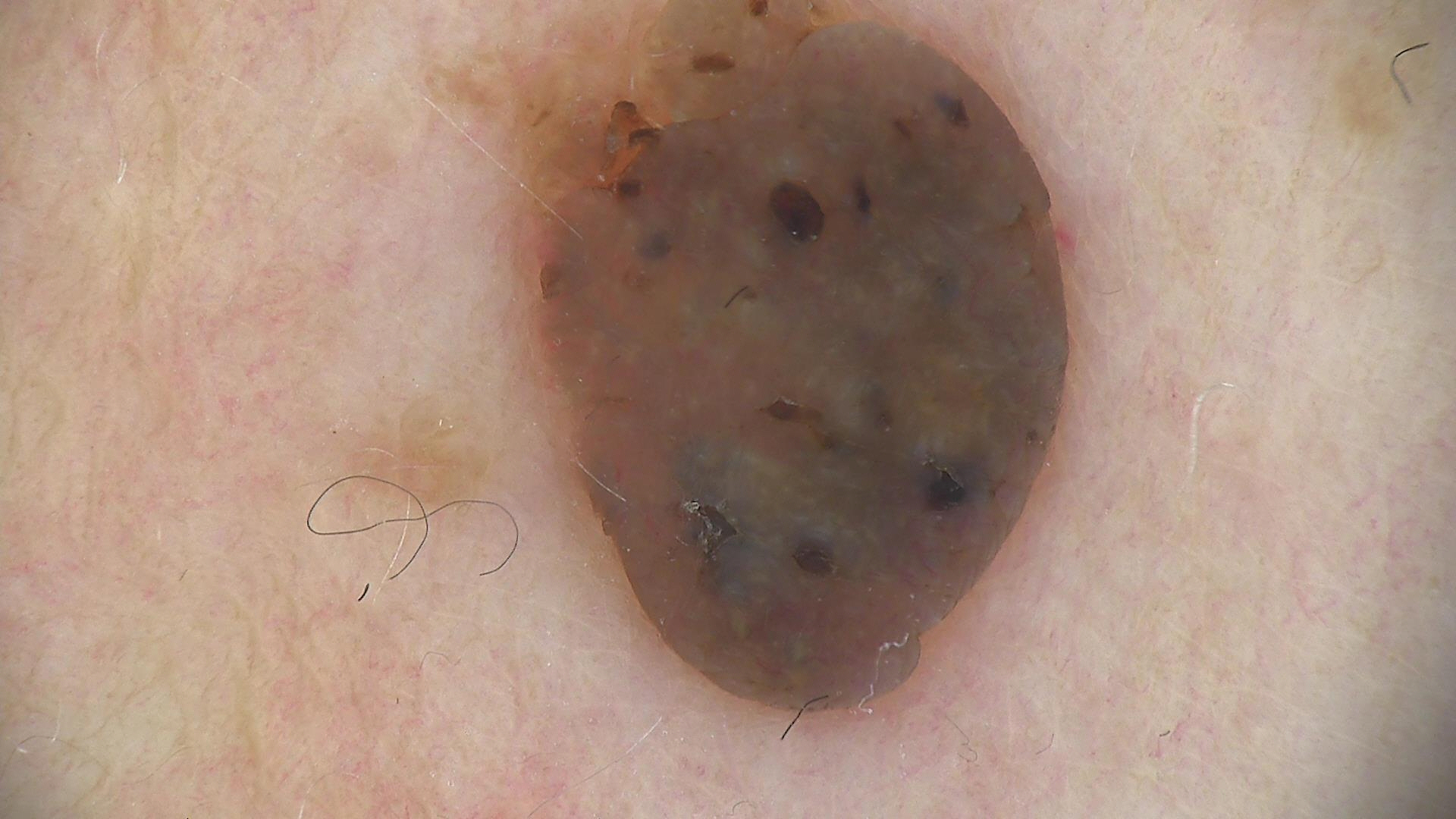Diagnosed as a seborrheic keratosis.